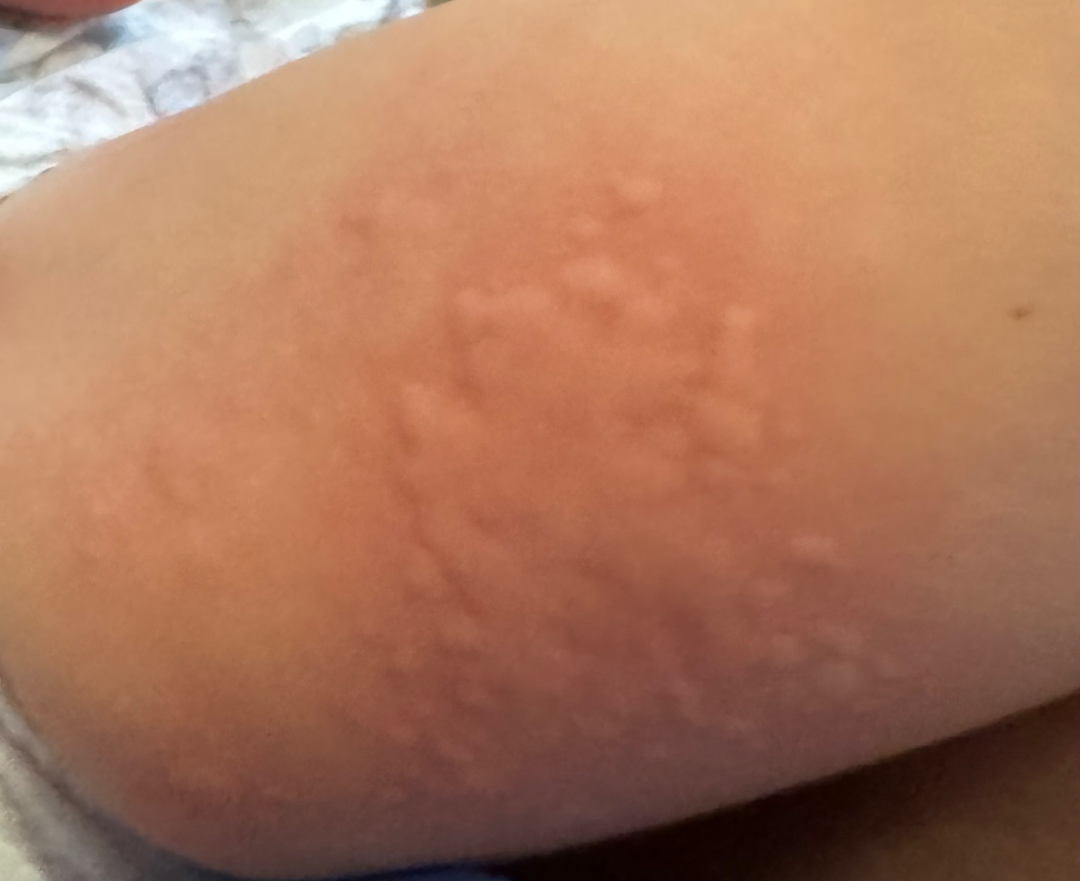skin tone=non-clinician graders estimated Monk skin tone scale 3 or 4; shot type=close-up; impression=most consistent with Urticaria.